Located on the head or neck; the patient considered this a rash; this image was taken at a distance; reported lesion symptoms include enlargement and itching; skin tone: Fitzpatrick phototype II; texture is reported as raised or bumpy; the condition has been present for less than one week.
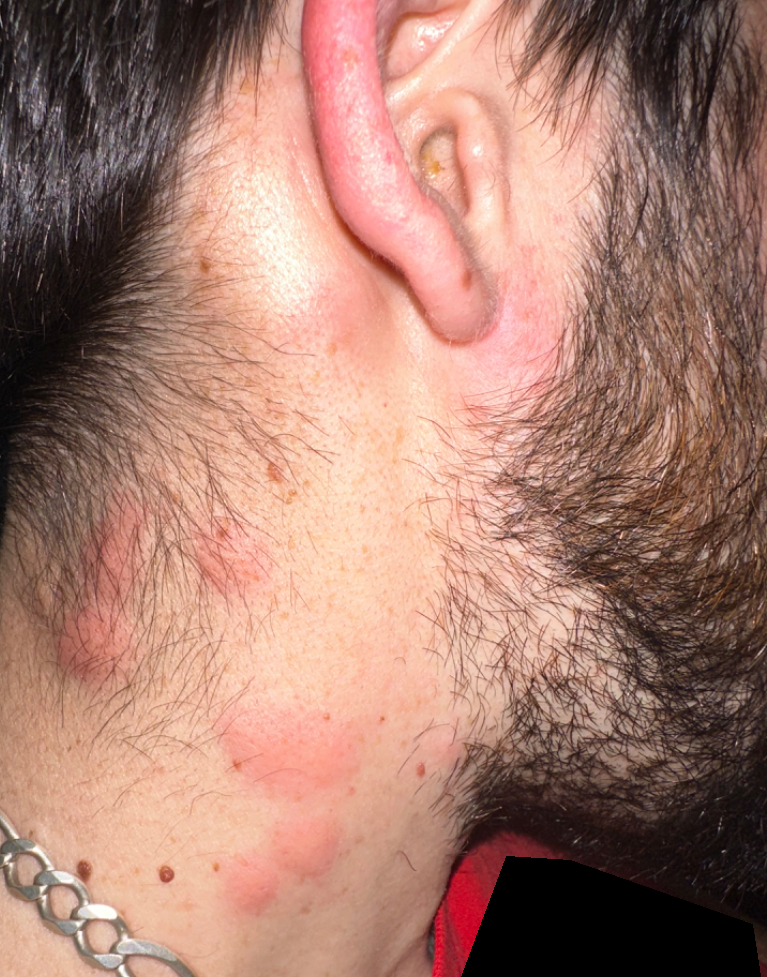differential diagnosis=the leading consideration is Urticaria.